An image taken at a distance · male subject, age 60–69 · the lesion involves the arm, back of the torso, head or neck and leg:
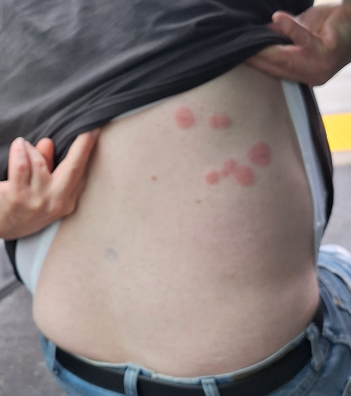Findings: The reviewing dermatologist's impression was: in keeping with Insect Bite.